A female subject 78 years of age · the chart records alcohol use and no pesticide exposure · a smartphone photograph of a skin lesion · the patient is FST II.
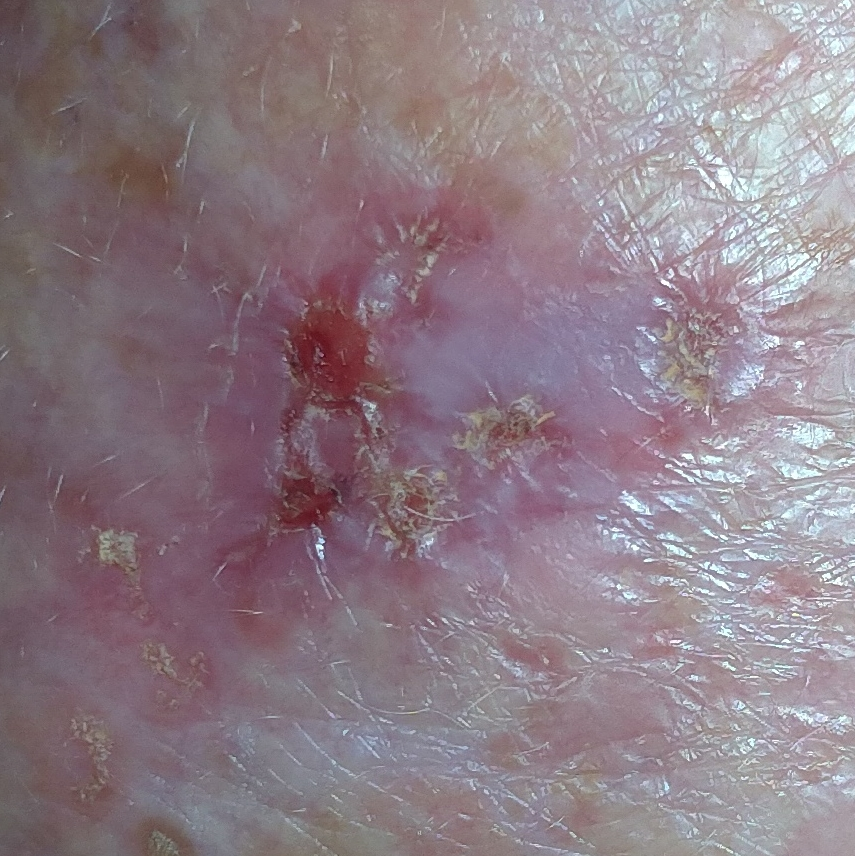site = a forearm | lesion diameter = approx. 20 × 15 mm | patient-reported symptoms = bleeding, itching, pain, elevation | pathology = basal cell carcinoma (biopsy-proven).